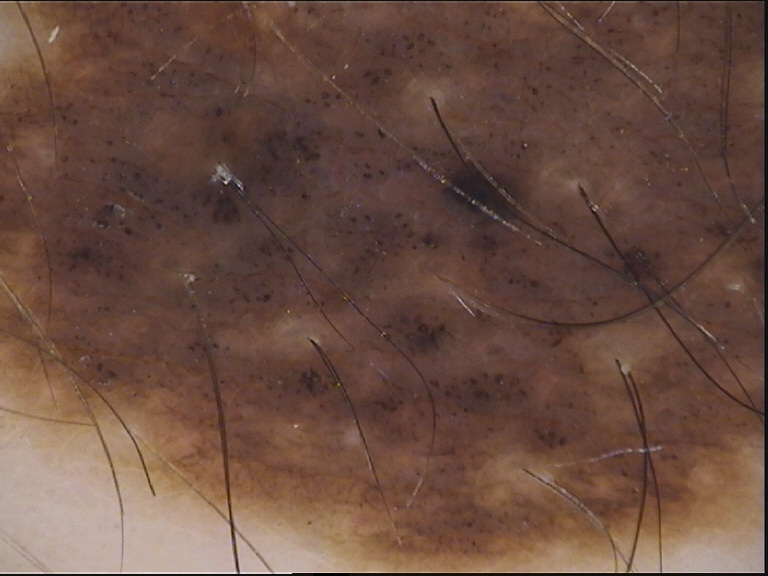Labeled as a congenital compound nevus.